Dermoscopy of a skin lesion — 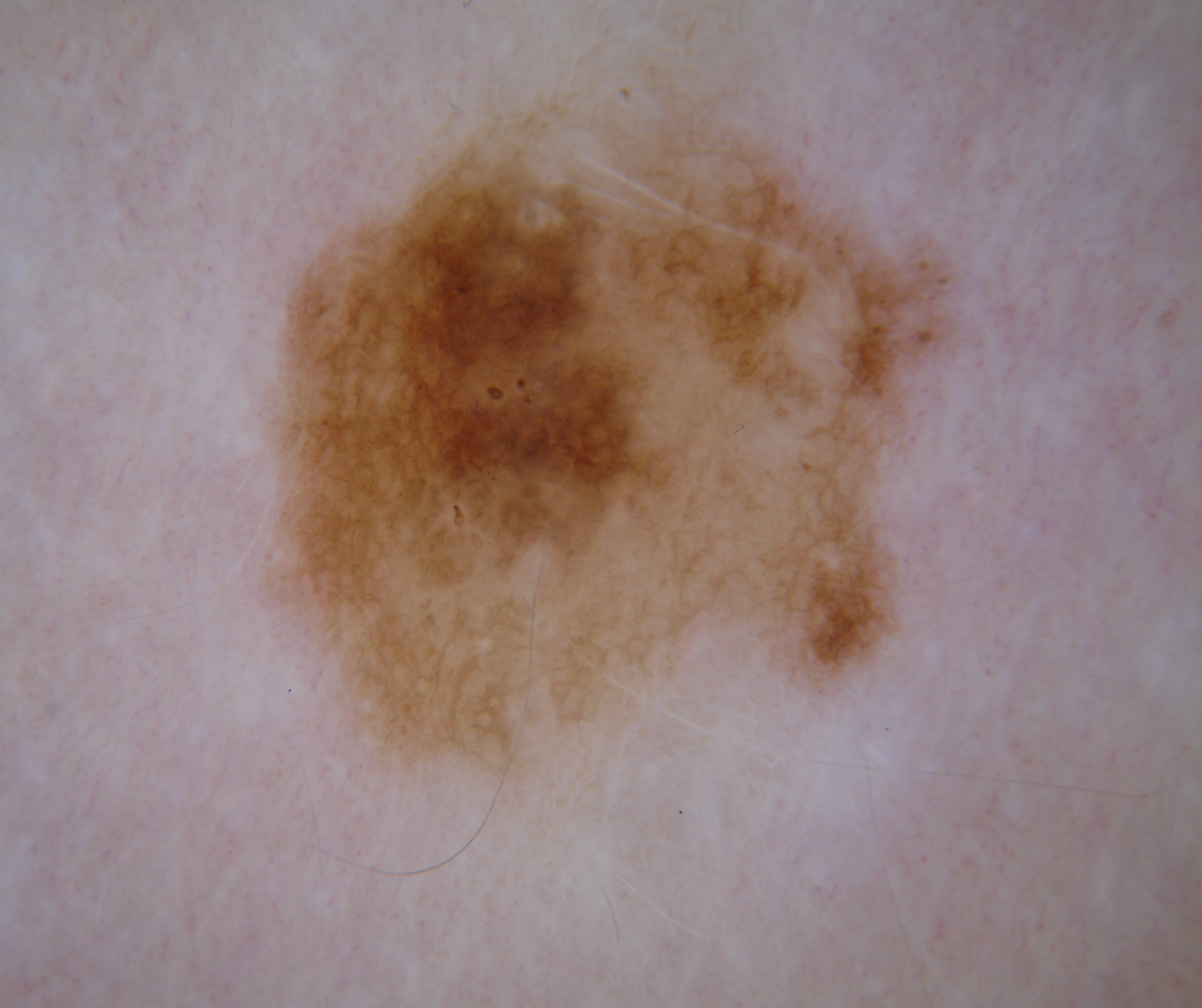<case>
<dermoscopic_features>
  <present>pigment network, globules</present>
  <absent>milia-like cysts, negative network, streaks</absent>
</dermoscopic_features>
<lesion_extent>moderate</lesion_extent>
<lesion_location>
  <bbox_xyxy>270, 46, 966, 785</bbox_xyxy>
</lesion_location>
<diagnosis>
  <name>melanocytic nevus</name>
  <malignancy>benign</malignancy>
  <lineage>melanocytic</lineage>
  <provenance>clinical</provenance>
</diagnosis>
</case>